Located on the arm and head or neck; the photo was captured at an angle.
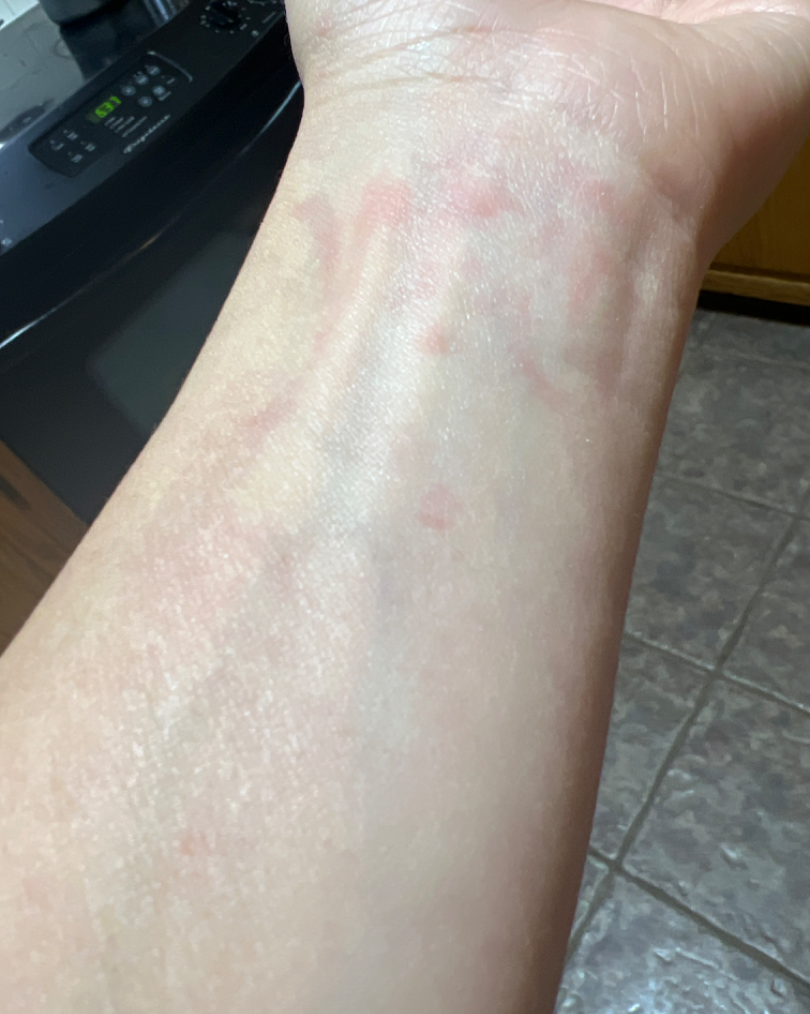| feature | finding |
|---|---|
| assessment | Insect Bite (possible); Irritant Contact Dermatitis (possible); Allergic Contact Dermatitis (possible) |